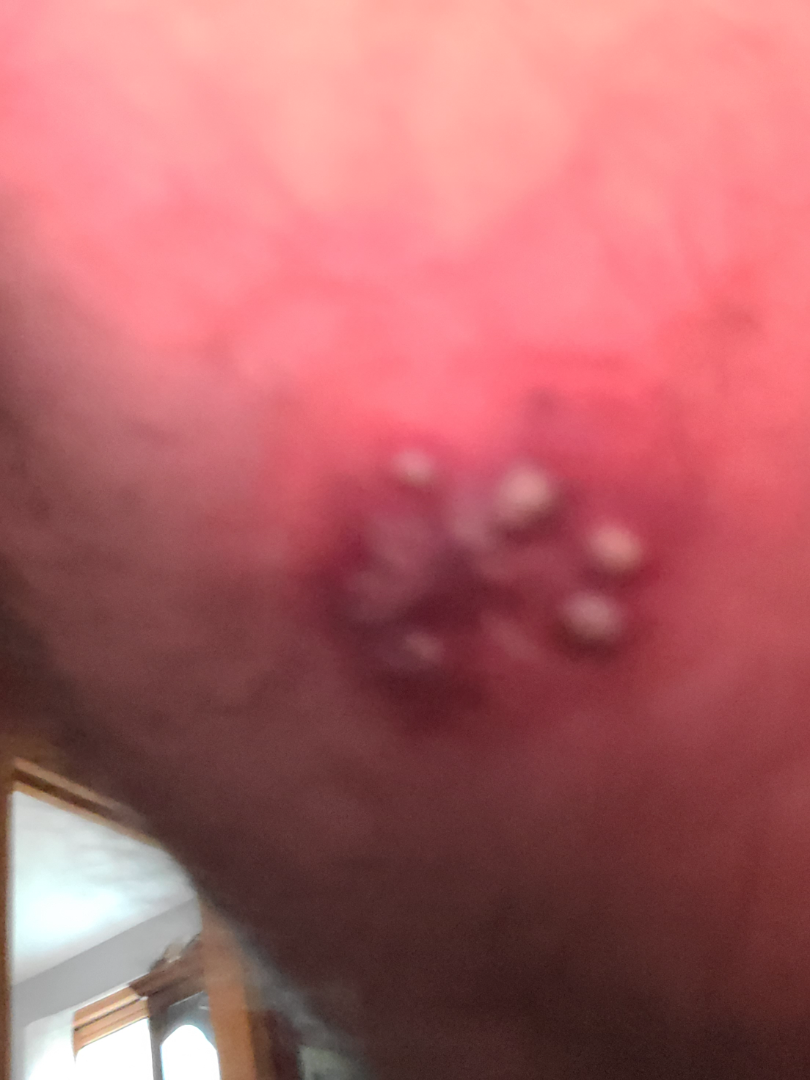  assessment: not assessable
  body_site: leg
  shot_type: close-up
  patient: male, age 60–69